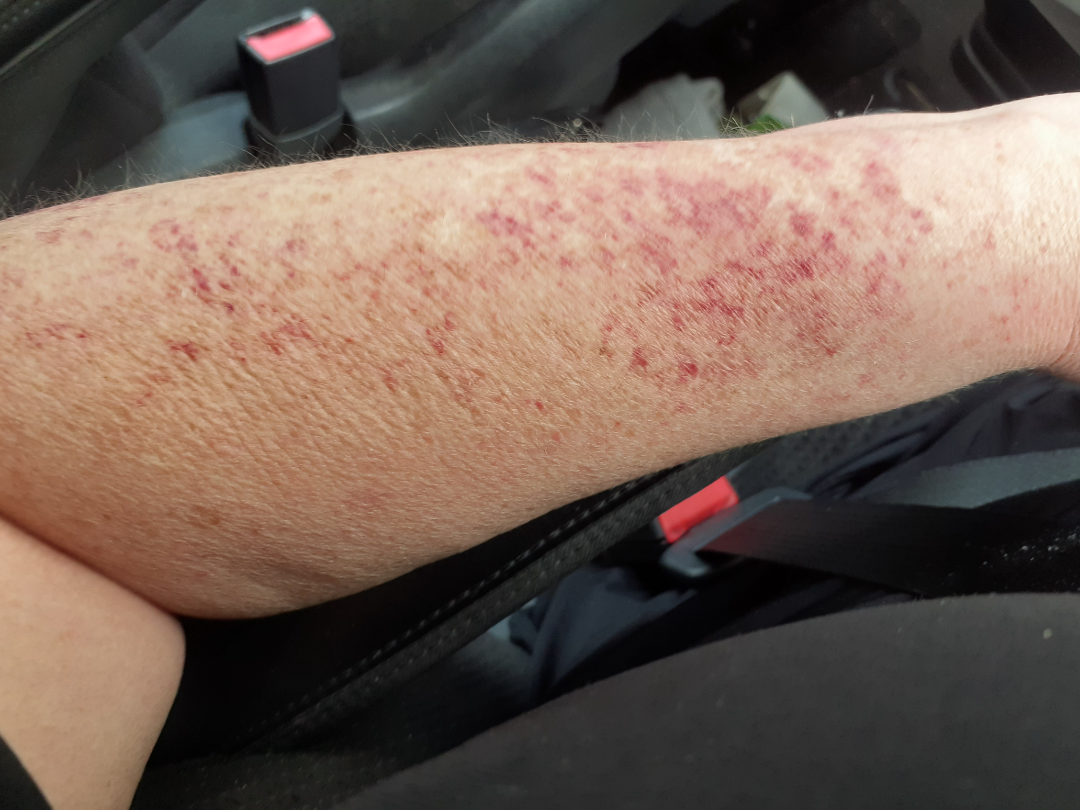shot_type: close-up
patient: female, age 40–49
body_site: arm
differential:
  leading:
    - Purpura